An image taken at a distance. Reported lesion symptoms include itching and burning. The lesion involves the arm. Self-categorized by the patient as a rash. The patient notes the condition has been present for less than one week. Skin tone: FST IV. The lesion is described as raised or bumpy and fluid-filled:
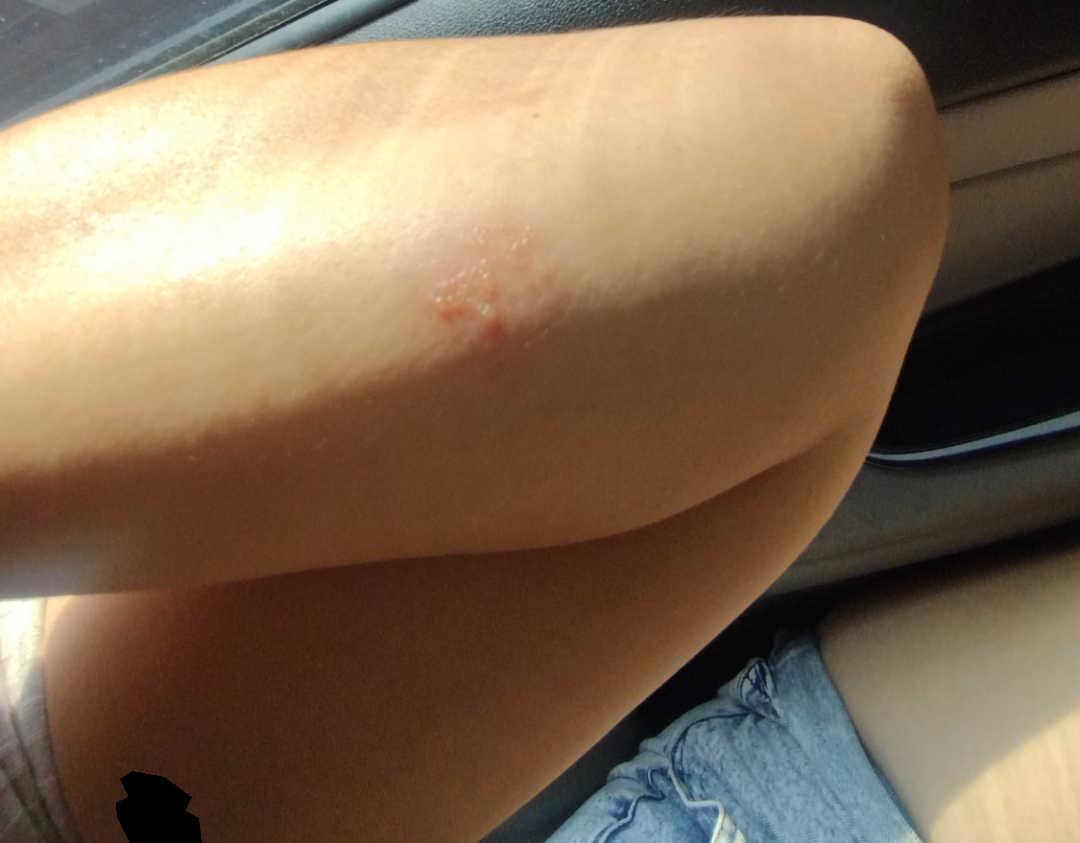Findings: Reviewed remotely by one dermatologist: the differential, in no particular order, includes Allergic Contact Dermatitis and Herpes Simplex.